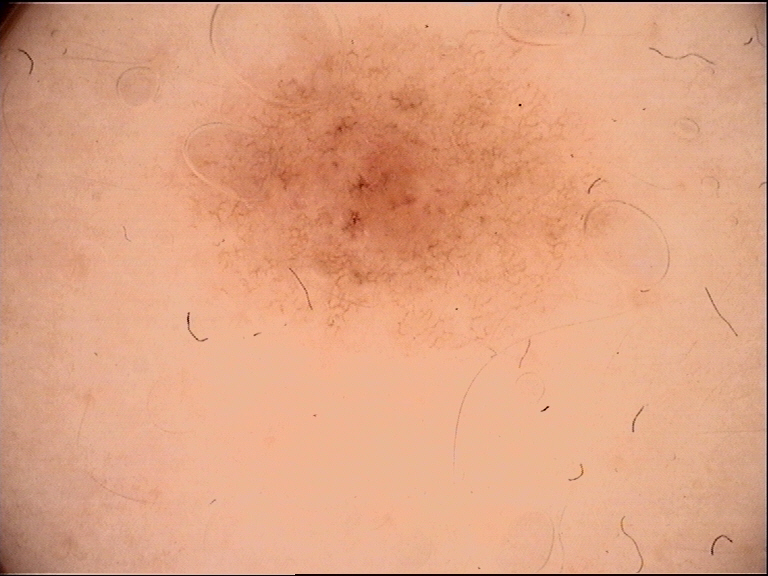Findings:
* assessment: dysplastic junctional nevus (expert consensus)